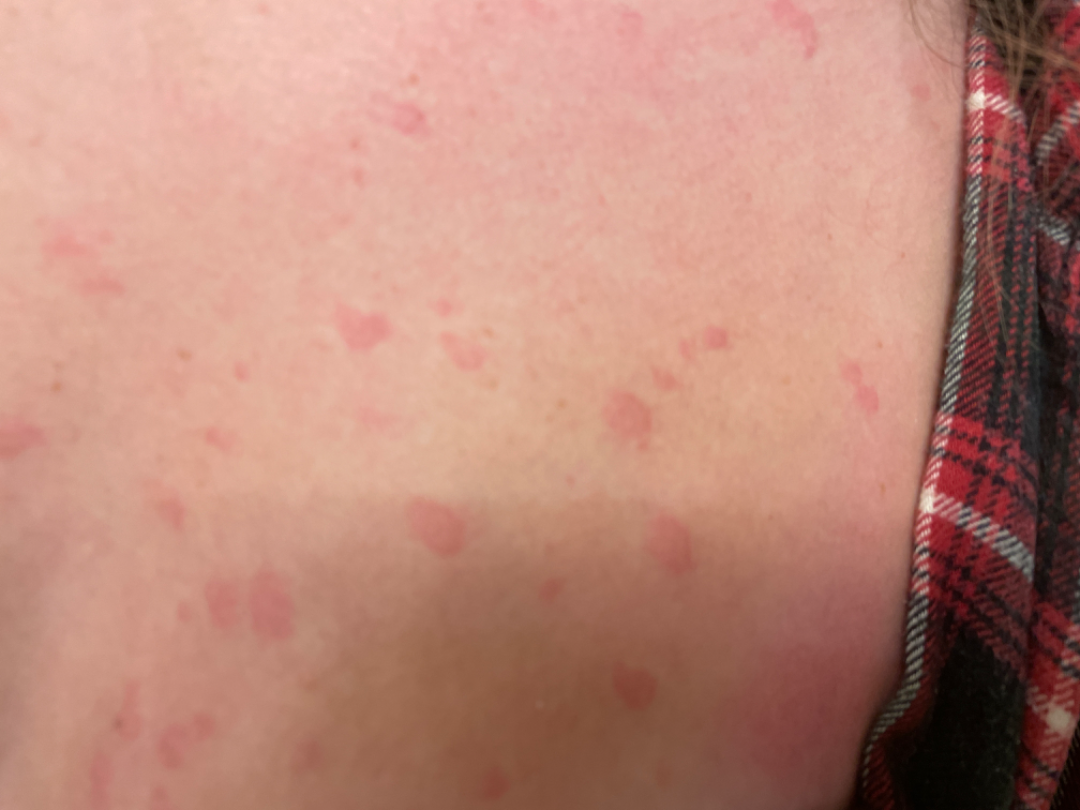assessment: indeterminate; view: close-up; affected area: front of the torso, arm, head or neck and back of the torso; contributor: female, age 18–29.